Recorded as Fitzpatrick II; a female subject in their mid- to late 50s.
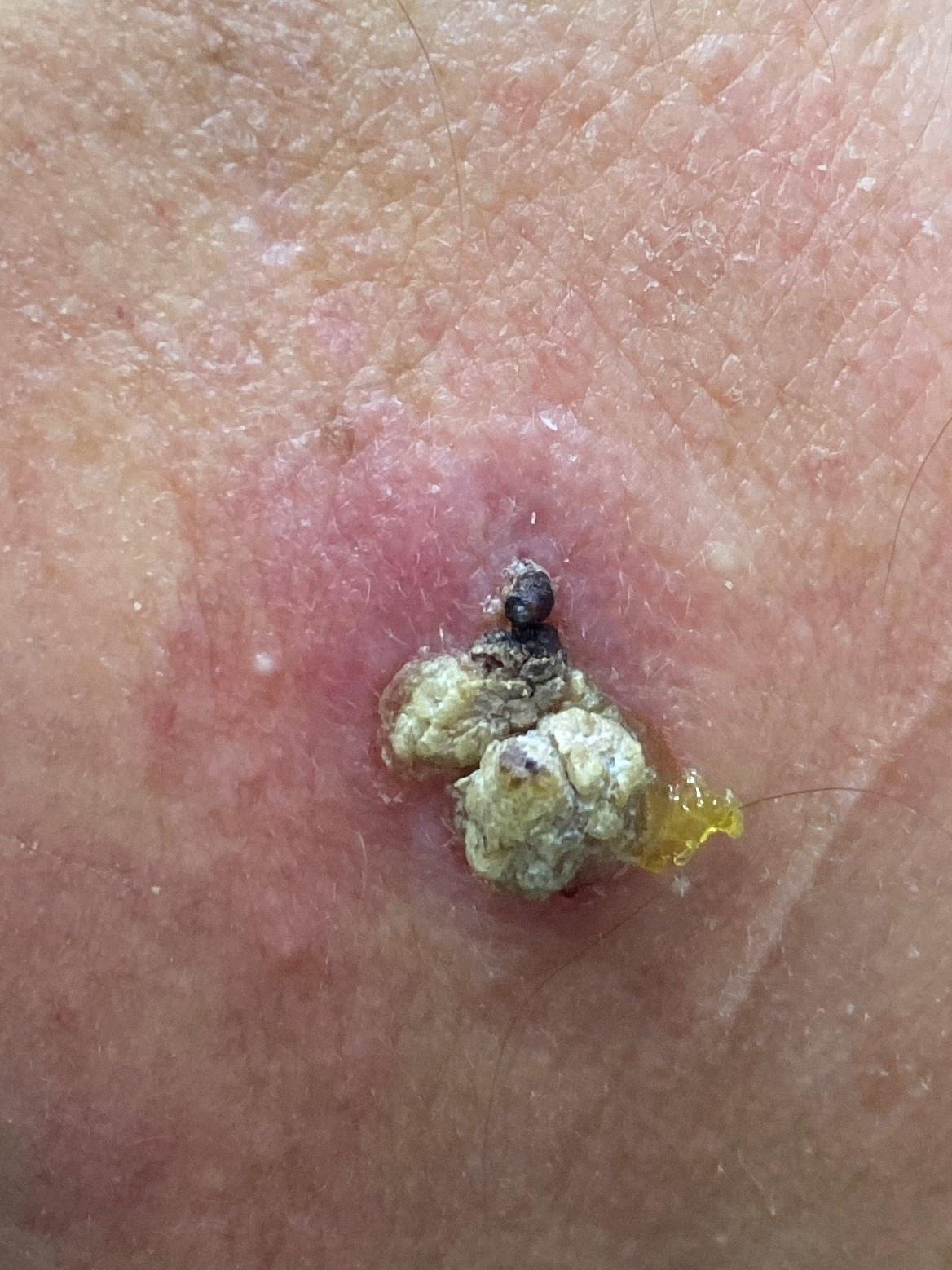Image and clinical context:
Located on the head or neck.
Pathology:
The biopsy diagnosis was a malignant, epidermal lesion — a squamous cell carcinoma.